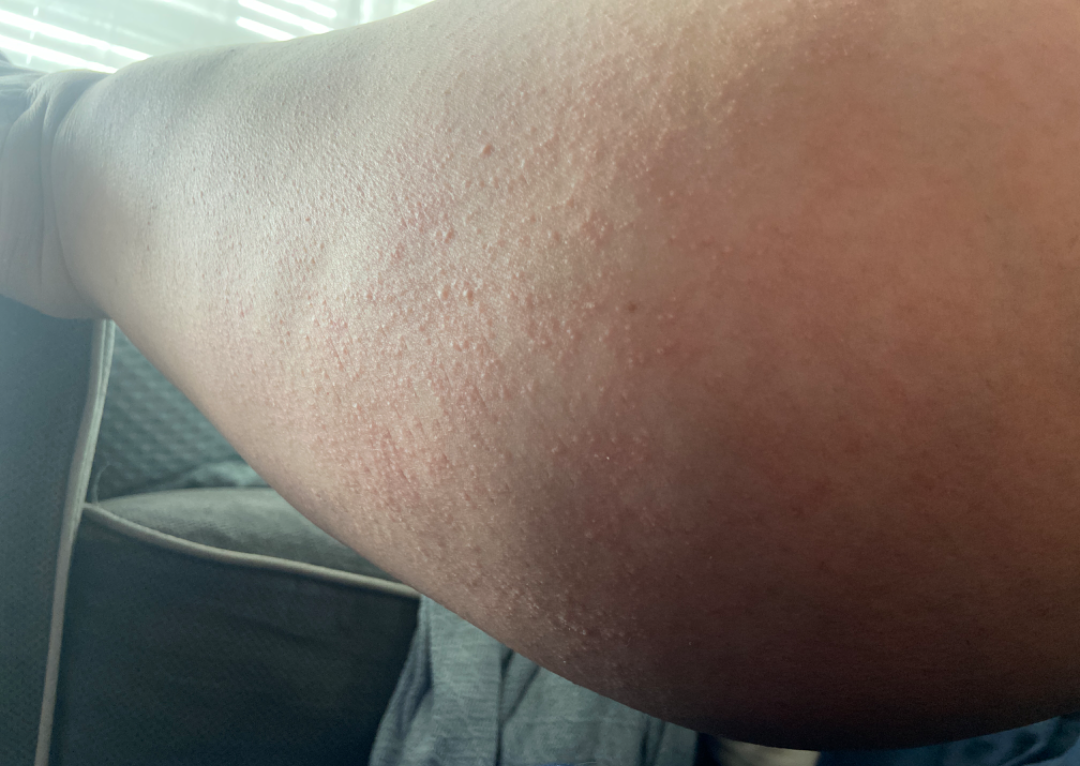differential diagnosis = reviewed remotely by three dermatologists: most consistent with Keratosis pilaris; possibly Eczema; a remote consideration is Miliaria; less likely is Folliculitis.